A female patient approximately 45 years of age. A skin lesion imaged with a dermatoscope.
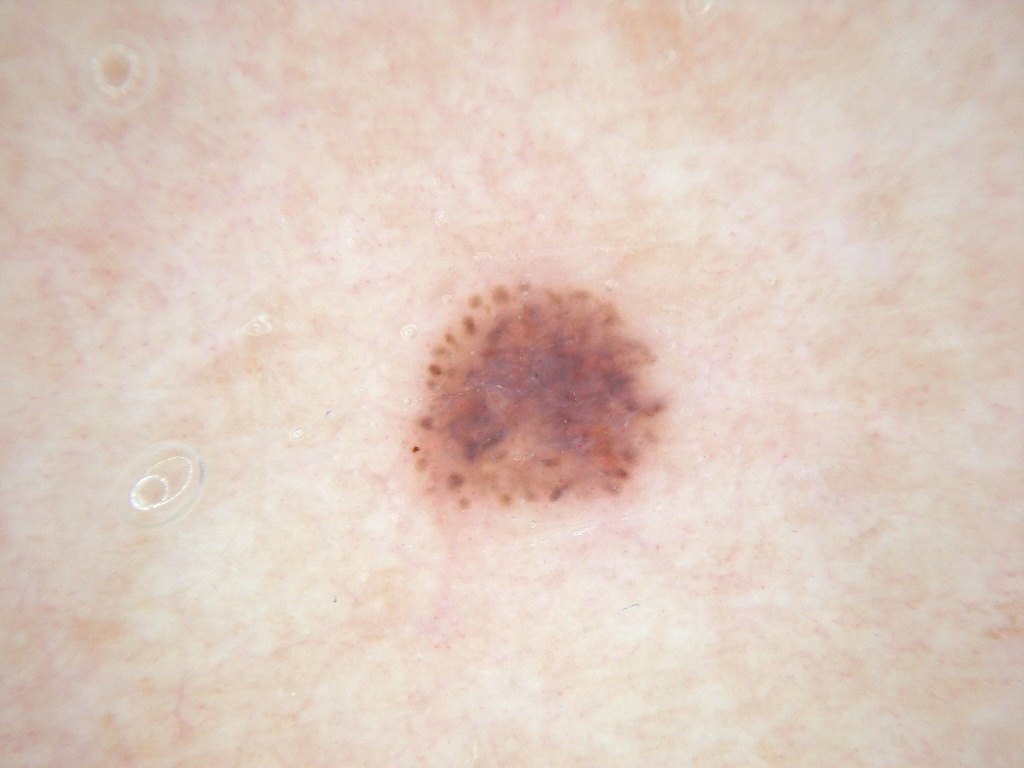Dermoscopy demonstrates no globules, pigment network, milia-like cysts, negative network, or streaks.
As (left, top, right, bottom), lesion location: <box>402, 259, 673, 525</box>.
The clinical diagnosis was a melanocytic nevus, a benign skin lesion.